The photograph was taken at an angle, the subject is a male aged 30–39, the affected area is the arm — 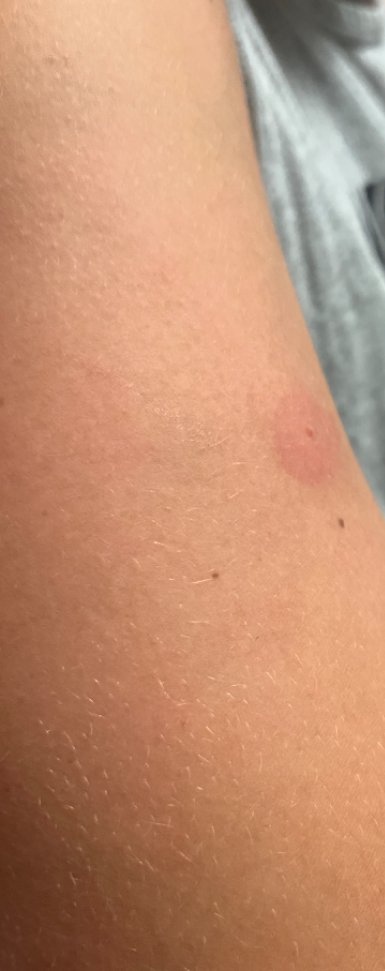{"assessment": "ungradable on photographic review", "duration": "less than one week", "patient_category": "skin that appeared healthy to them", "symptoms": ["itching", "bothersome appearance"]}